A male subject, aged approximately 45. A dermatoscopic image of a skin lesion — 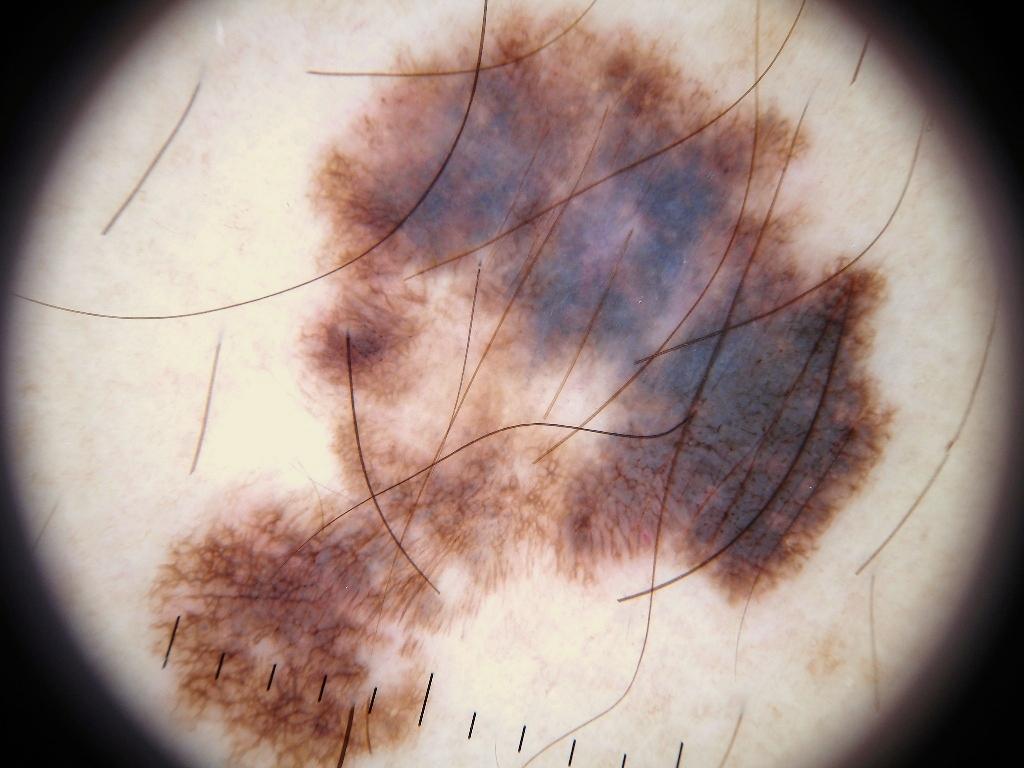dermoscopic findings: pigment network and streaks | bounding box: (131, 0, 911, 766) | assessment: a melanoma, a malignancy.